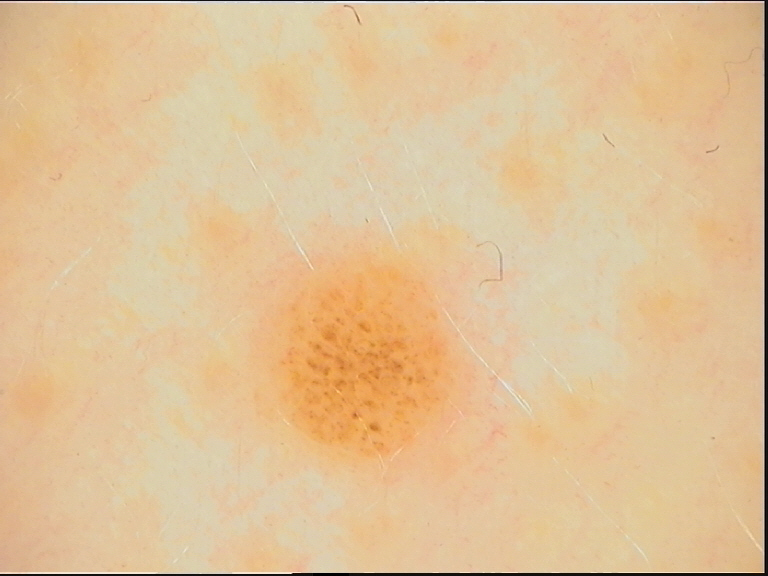Q: What kind of image is this?
A: dermoscopy
Q: What is this lesion?
A: junctional nevus (expert consensus)